A dermatoscopic image of a skin lesion. A female subject, aged approximately 25: 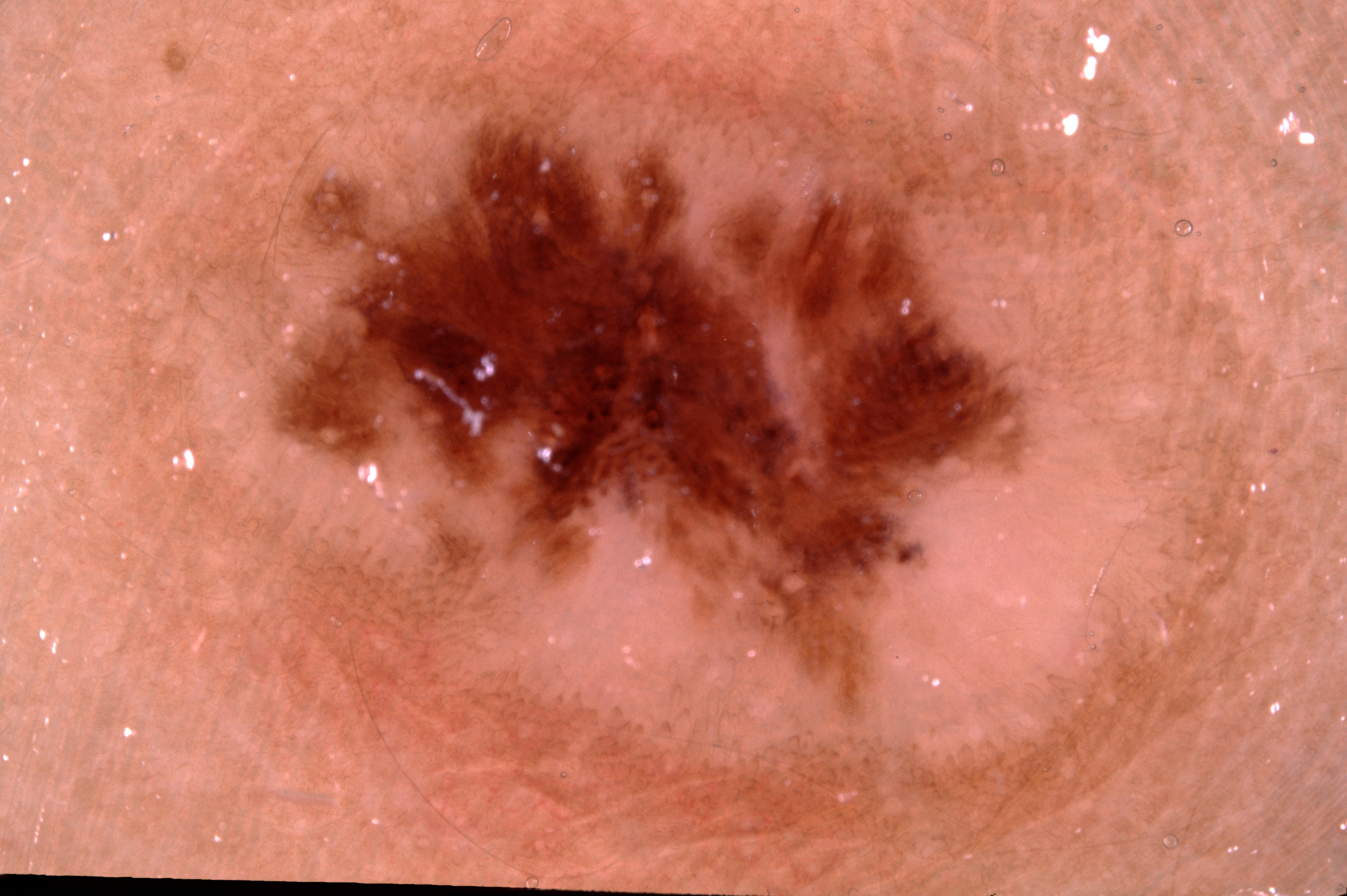Findings:
The lesion is located at x1=198, y1=38, x2=1265, y2=851. A prominent lesion filling much of the field. On dermoscopy, the lesion shows no pigment network, streaks, milia-like cysts, or negative network.
Conclusion:
The diagnostic assessment was a melanocytic nevus, a benign lesion.